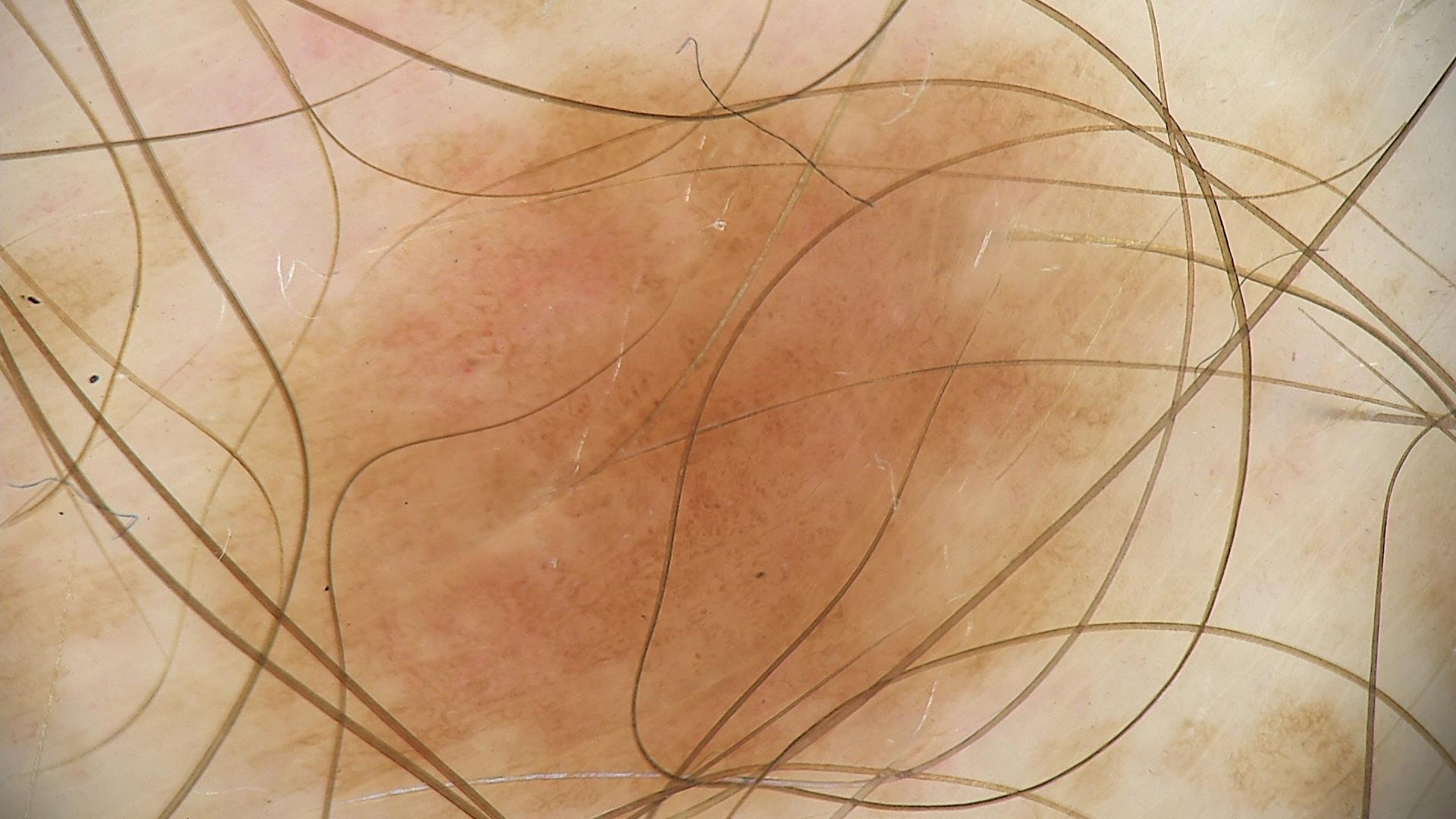Case:
• image · dermatoscopy
• diagnosis · compound nevus (expert consensus)